Present for one to four weeks; no constitutional symptoms were reported; the photograph is a close-up of the affected area; the patient described the issue as a rash; the back of the hand, leg and top or side of the foot are involved; the patient is a female aged 60–69; the lesion is associated with bothersome appearance: 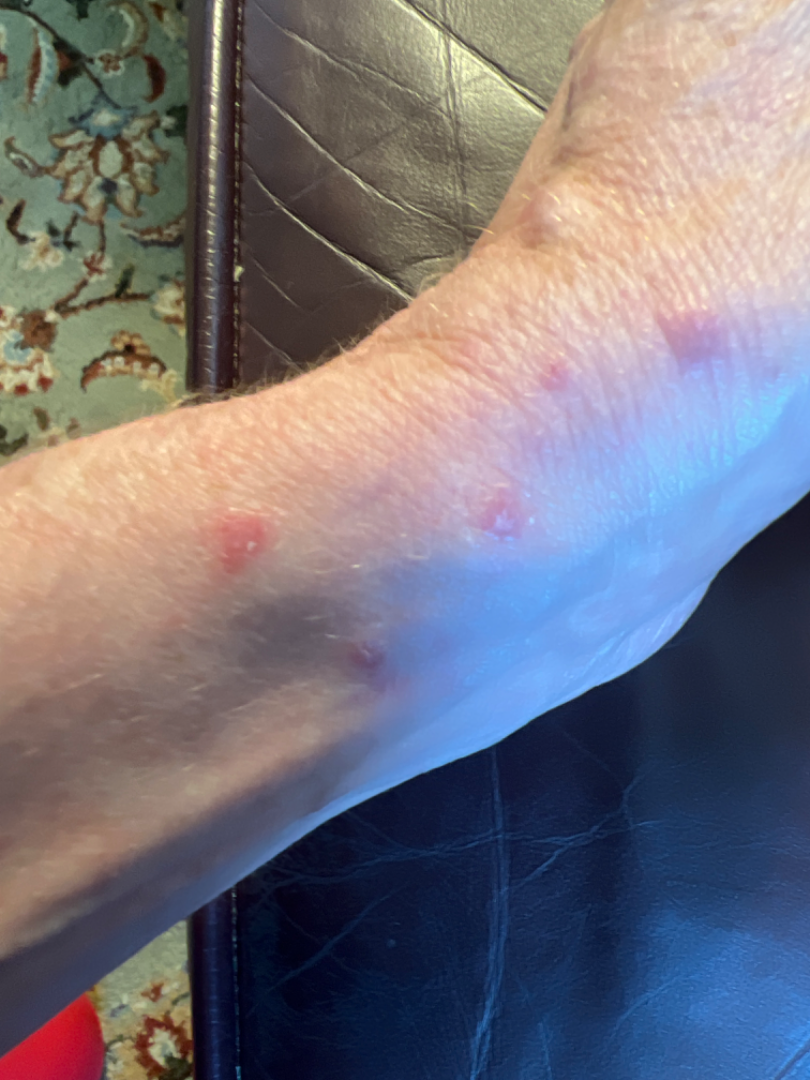On photographic review by a dermatologist: Impetigo (leading); Skin infection (considered); Lichen planus/lichenoid eruption (considered).